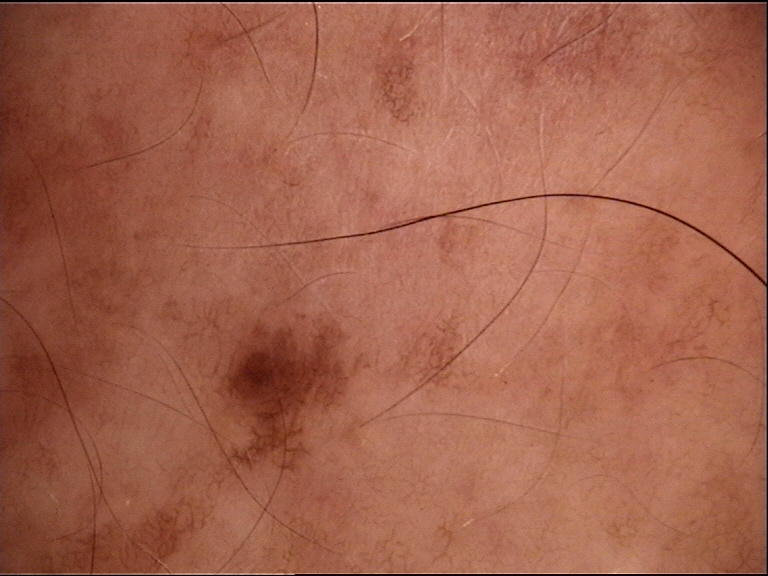<case>
  <image>dermatoscopy</image>
  <diagnosis>
    <name>dysplastic junctional nevus</name>
    <code>jd</code>
    <malignancy>benign</malignancy>
    <super_class>melanocytic</super_class>
    <confirmation>expert consensus</confirmation>
  </diagnosis>
</case>